A dermoscopy image of a single skin lesion: 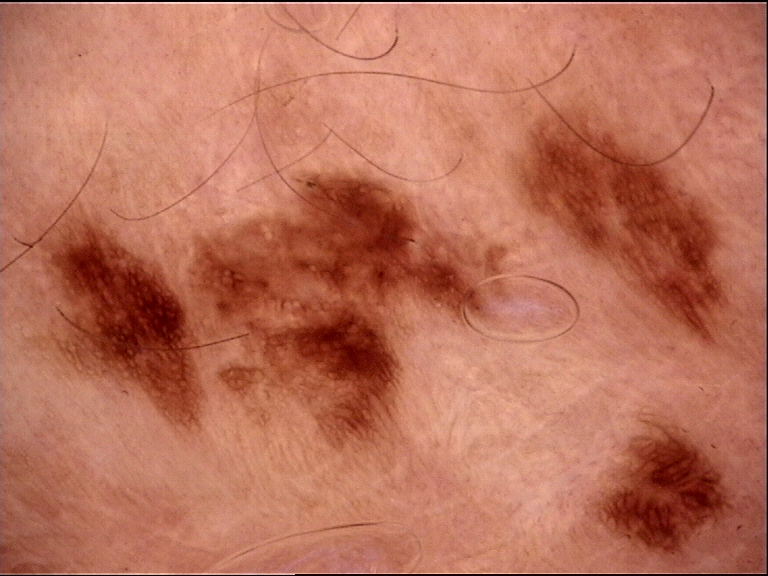Case:
– label: recurrent nevus (expert consensus)